The contributor is male · a close-up photograph · the contributor notes the condition has been present for one to four weeks · the contributor notes the lesion is raised or bumpy and rough or flaky · the head or neck, leg, front of the torso and arm are involved · no associated lesion symptoms were reported — 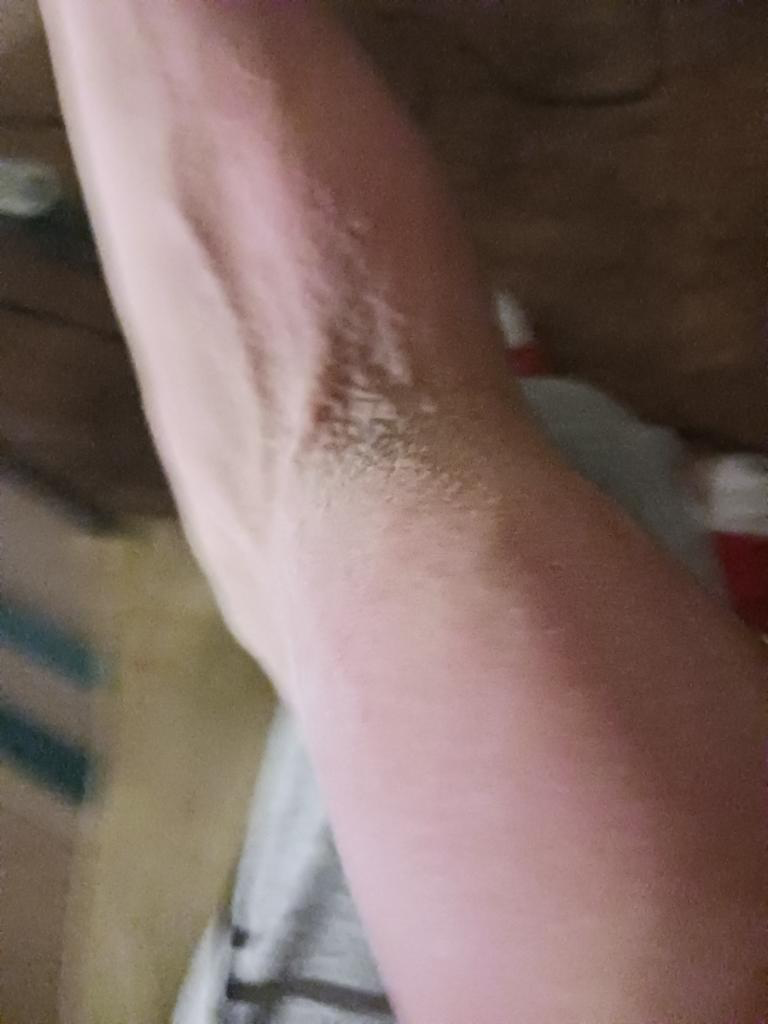Findings:
The skin condition could not be confidently assessed from this image.